Close-up view; the leg is involved:
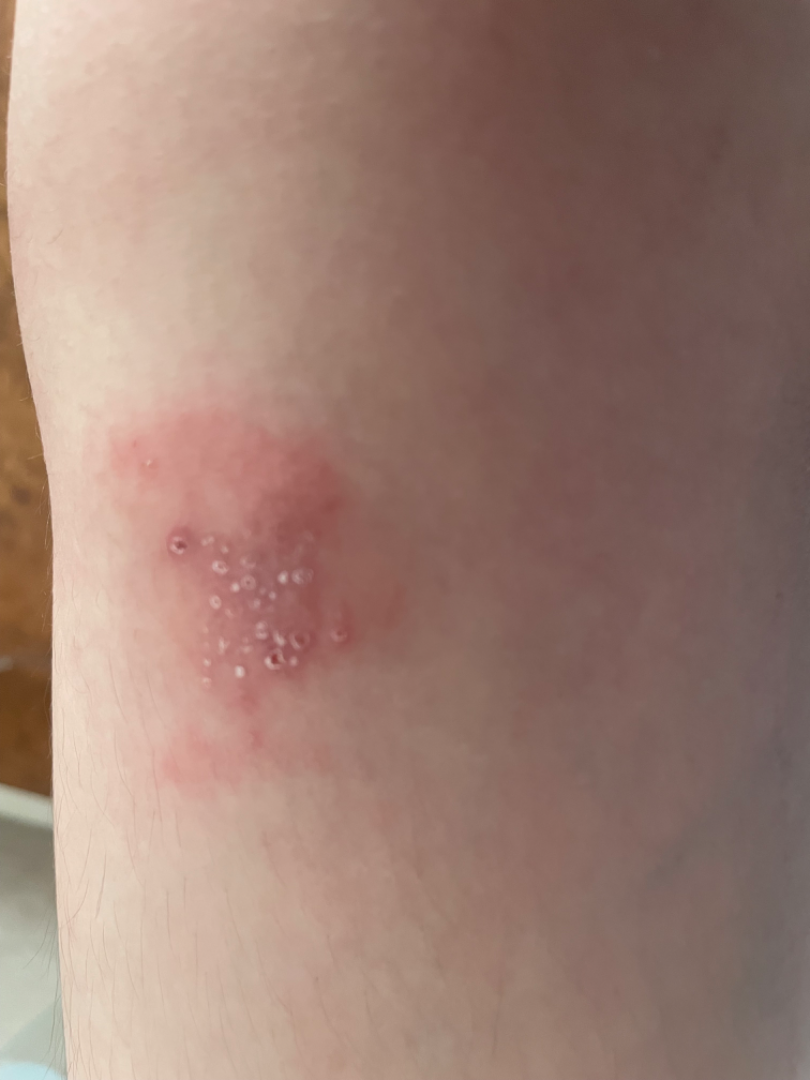assessment = unable to determine.